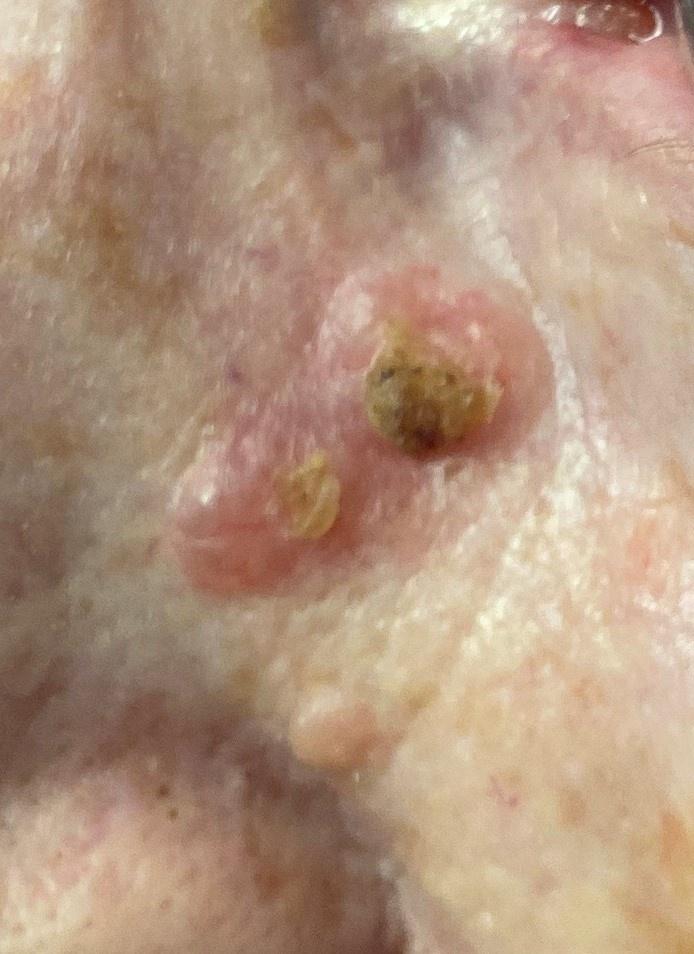A clinical photograph of a skin lesion.
Skin type II.
Biopsy-confirmed as a basal cell carcinoma.